Referred with a clinical suspicion of seborrheic keratosis · dermoscopy of a skin lesion · the patient says their skin tans without first burning: 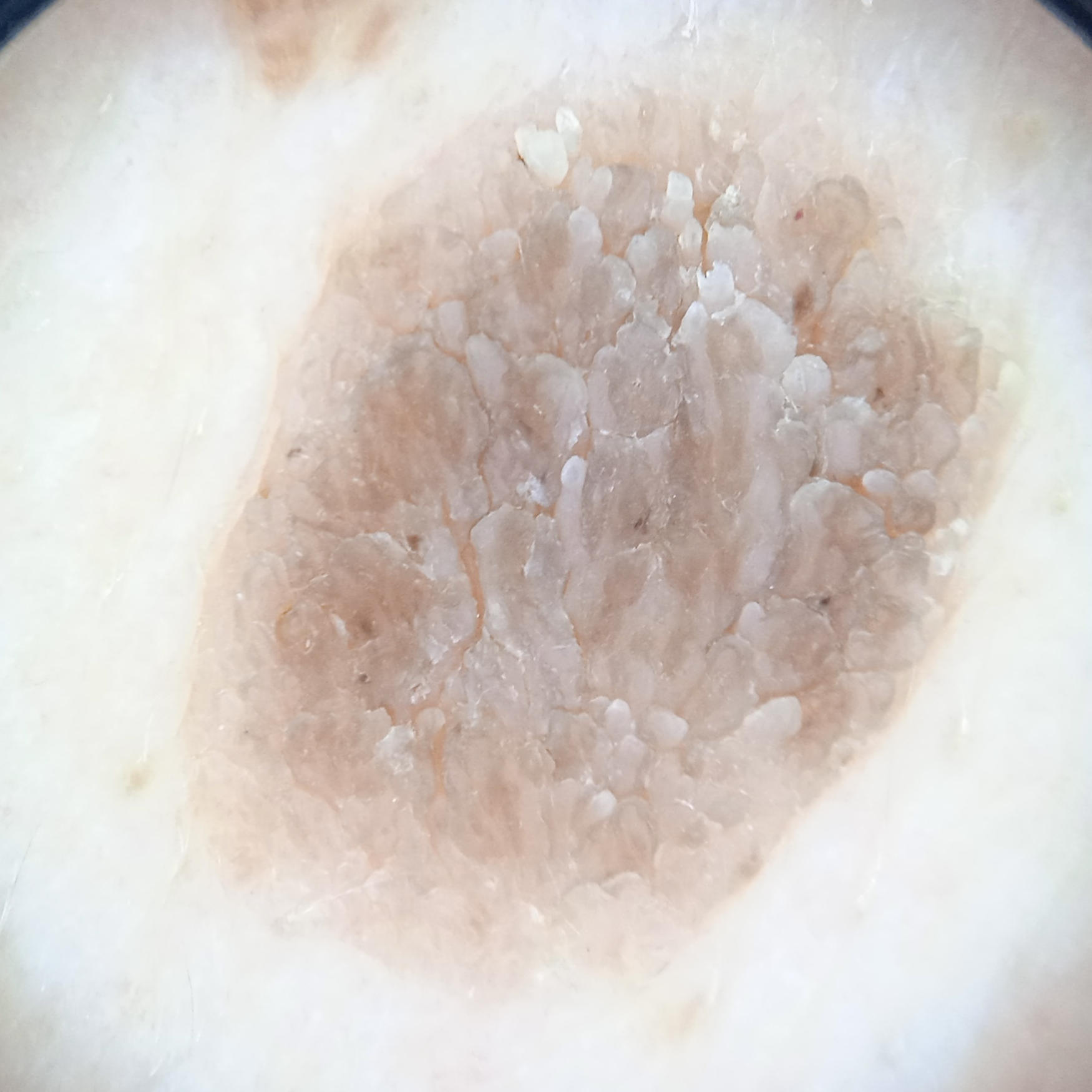The lesion involves the back. On independent review by four dermatologists, the agreed diagnosis was a seborrheic keratosis; the reviewers were fairly confident.